A dermatoscopic image of a skin lesion; a male patient aged approximately 75 — 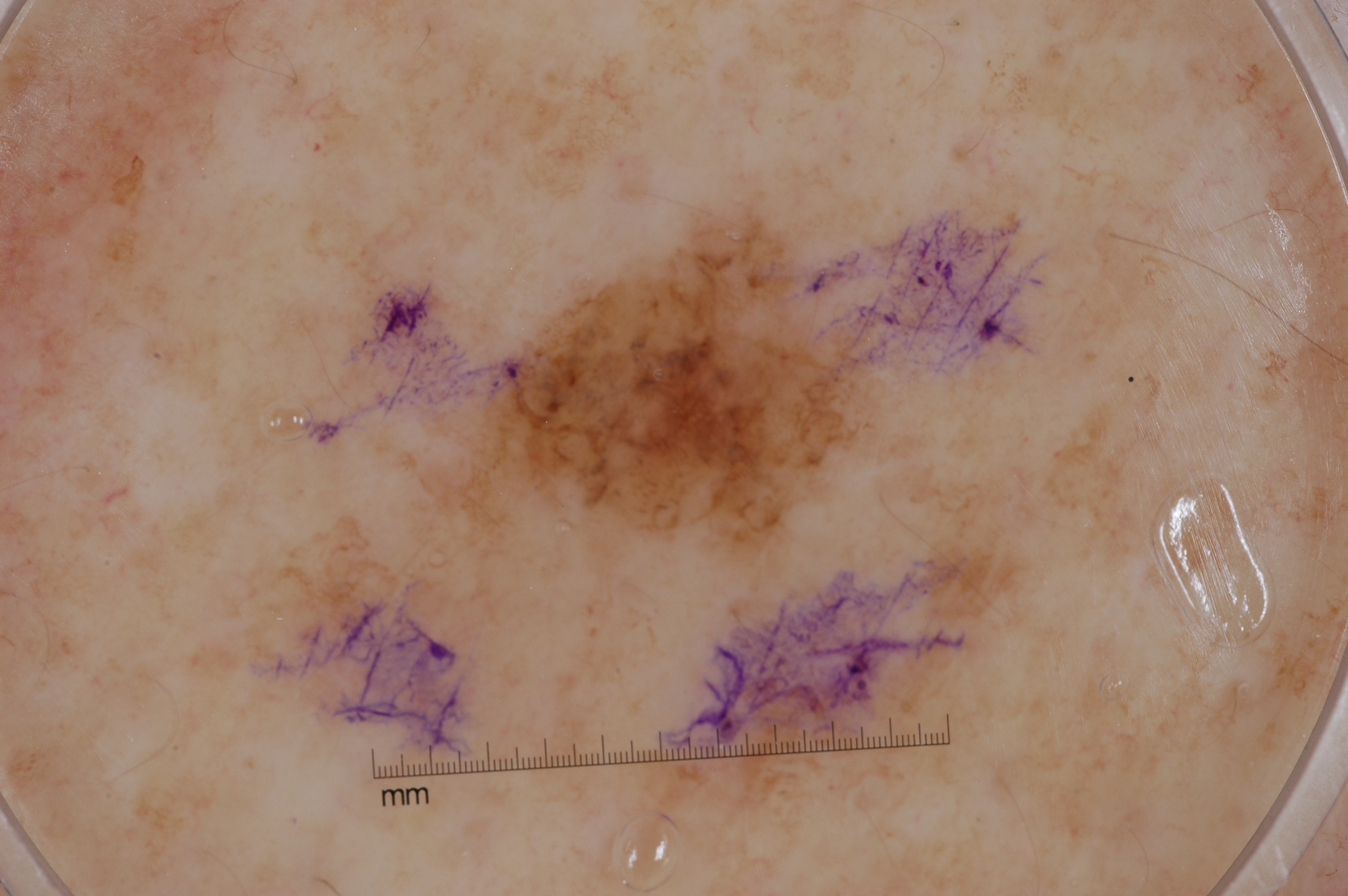Q: What does dermoscopy show?
A: pigment network
Q: Where is the lesion located?
A: left=394, top=161, right=953, bottom=619
Q: Lesion extent?
A: moderate
Q: What did the assessment conclude?
A: a melanoma